A male patient, aged 58-62 · a dermoscopic close-up of a skin lesion:
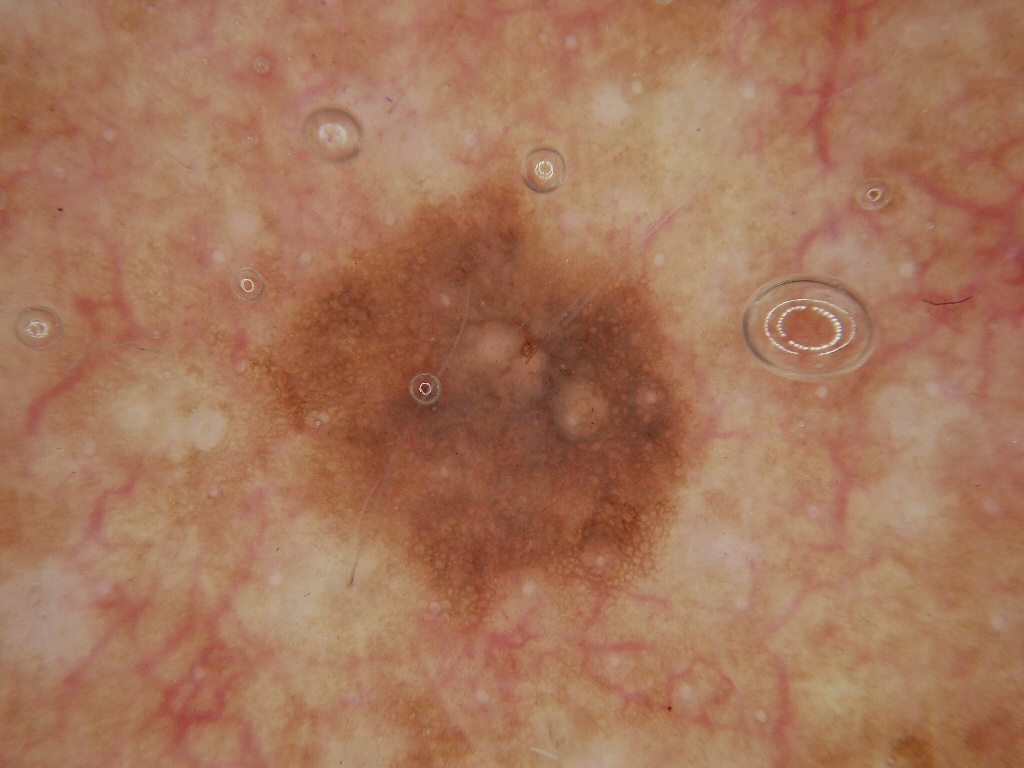• lesion extent — moderate
• lesion location — left=213, top=156, right=717, bottom=654
• dermoscopic pattern — milia-like cysts and pigment network
• diagnosis — a melanocytic nevus